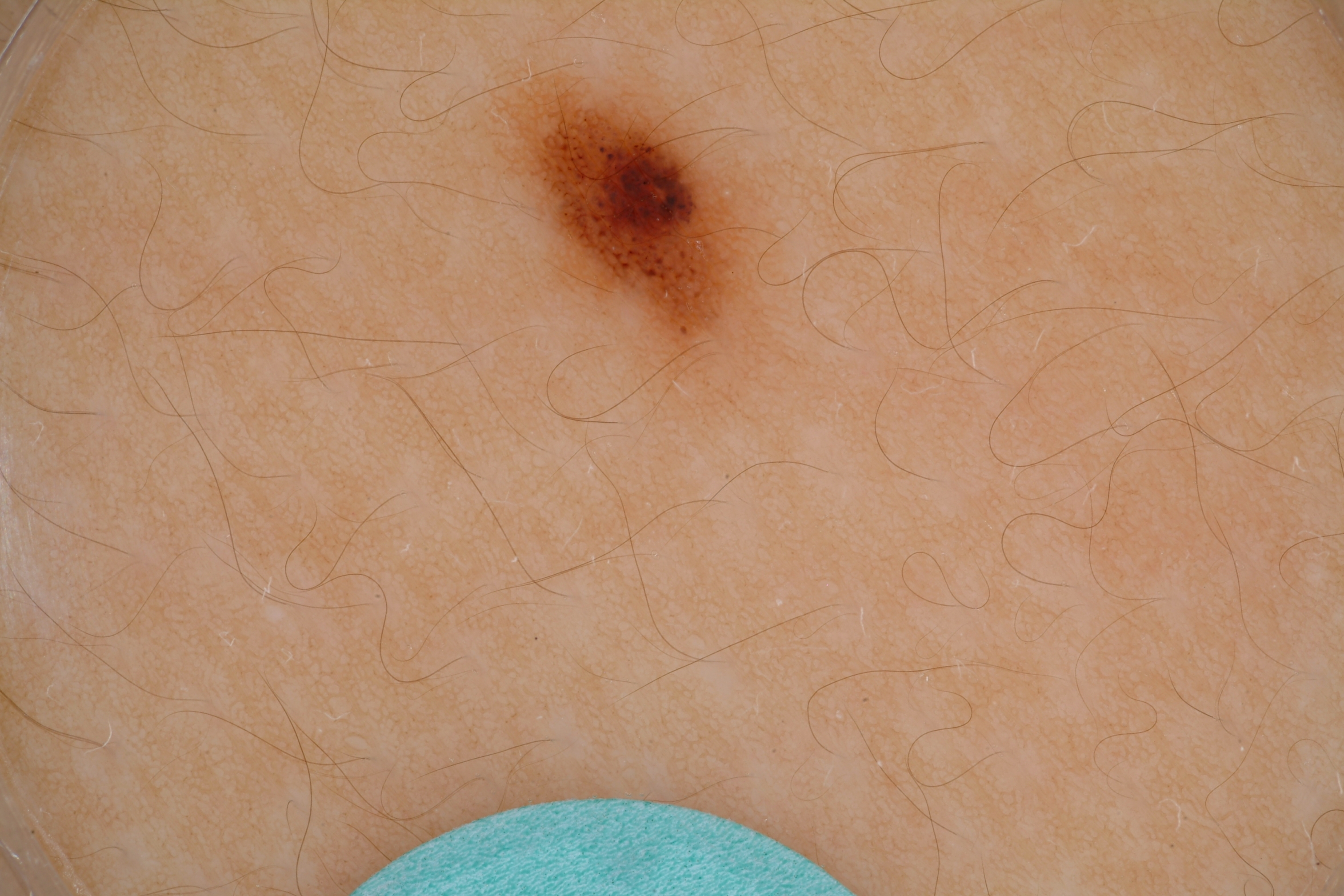Findings:
This is a dermoscopic photograph of a skin lesion. The lesion is bounded by [470, 55, 769, 379]. A small lesion within a wider field of skin. Dermoscopic examination shows milia-like cysts and pigment network.
Impression:
Clinically diagnosed as a melanocytic nevus.